A patient 69 years of age. A clinical photograph showing a skin lesion.
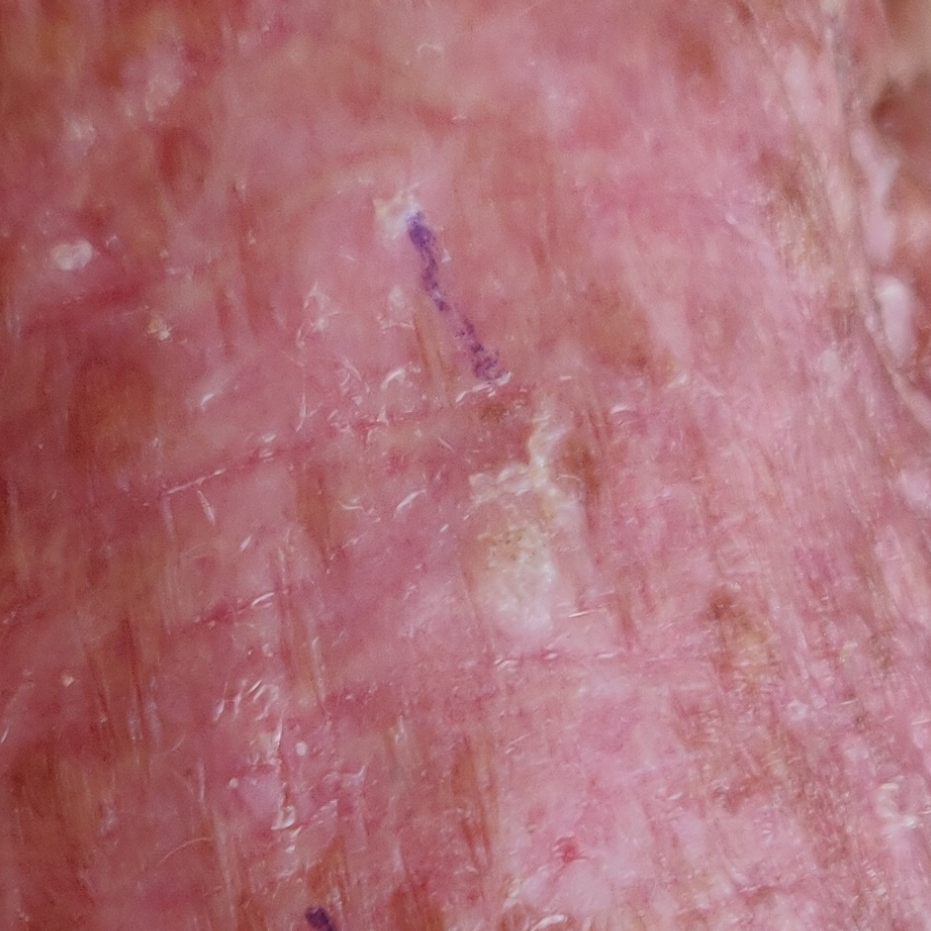The patient describes that the lesion itches and has grown. The clinical impression was an actinic keratosis.